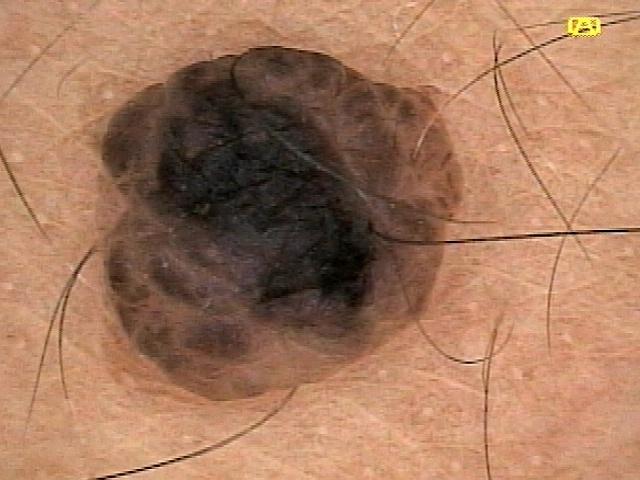patient = male, roughly 35 years of age; imaging = contact-polarized dermoscopy; anatomic site = a lower extremity; diagnostic label = Nevus (clinical impression).